The front of the torso, arm and leg are involved; close-up view; the subject is 18–29, female.
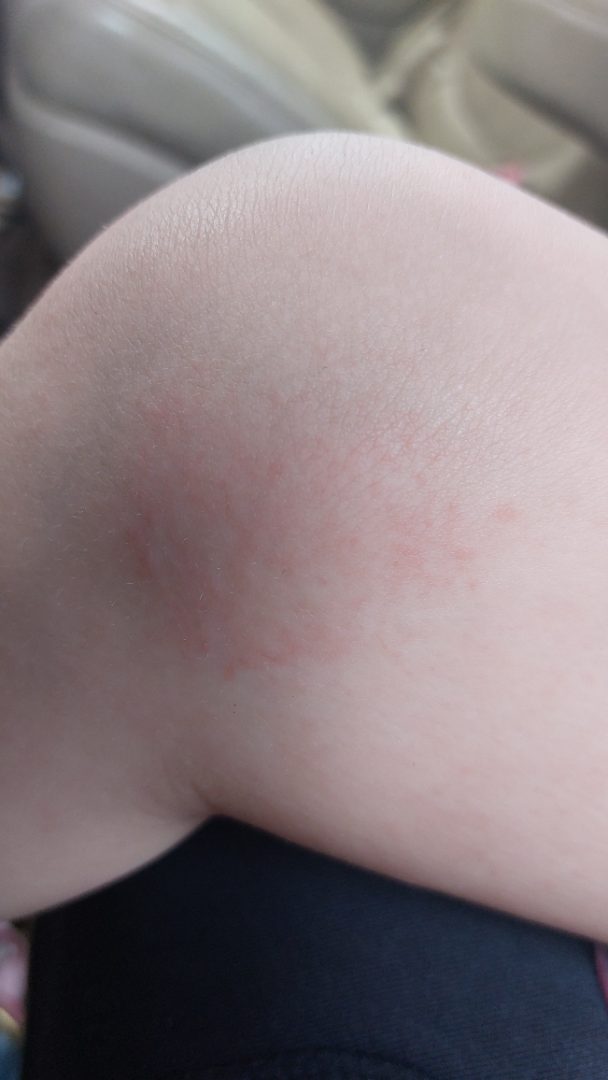Findings:
* assessment · unable to determine